A dermoscopic photograph of a skin lesion.
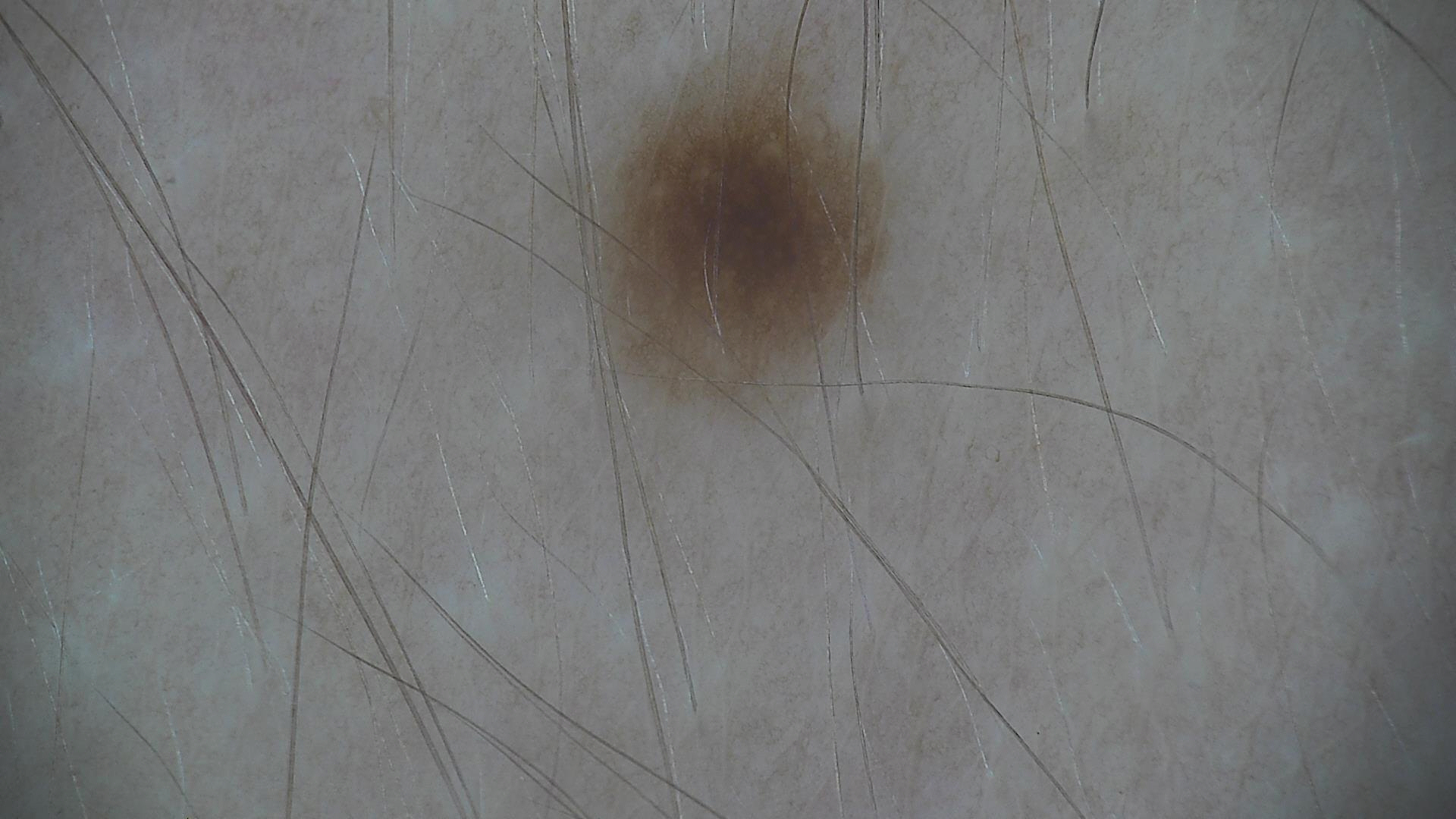Conclusion:
The diagnostic label was a dysplastic junctional nevus.